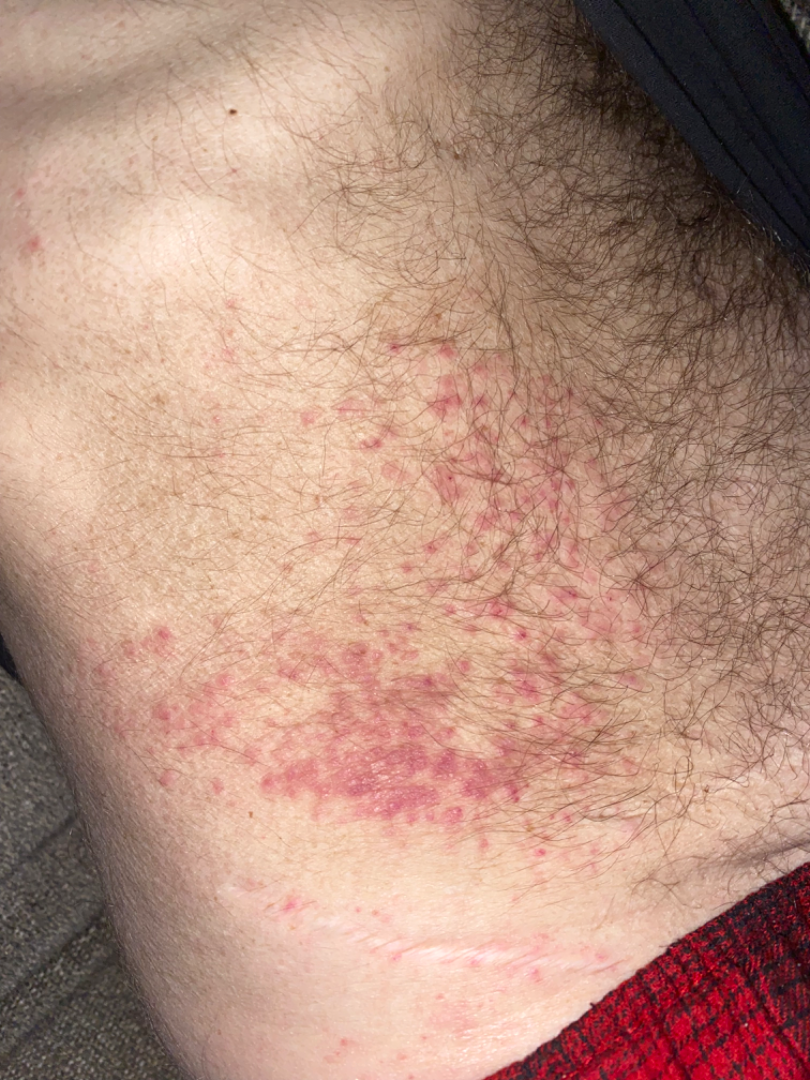Findings:
- view: close-up
- diagnostic considerations: most consistent with Eczema; possibly Allergic Contact Dermatitis